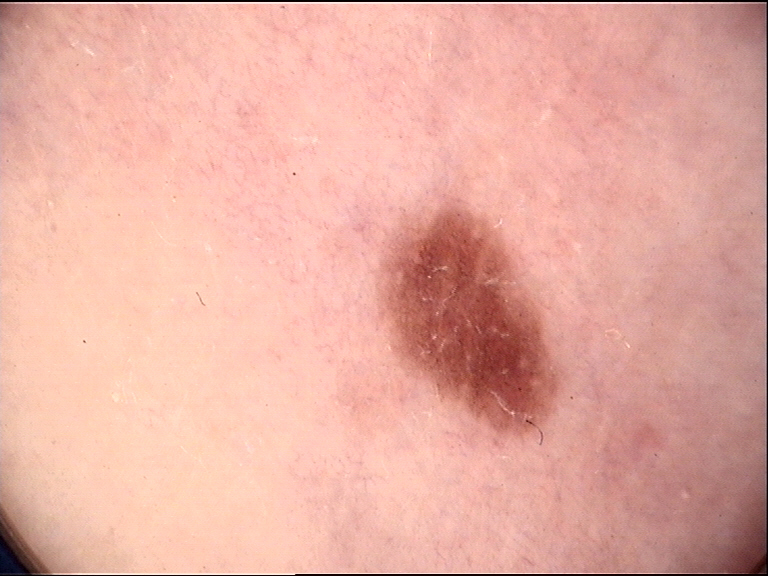| field | value |
|---|---|
| modality | dermoscopy |
| class | dysplastic junctional nevus (expert consensus) |